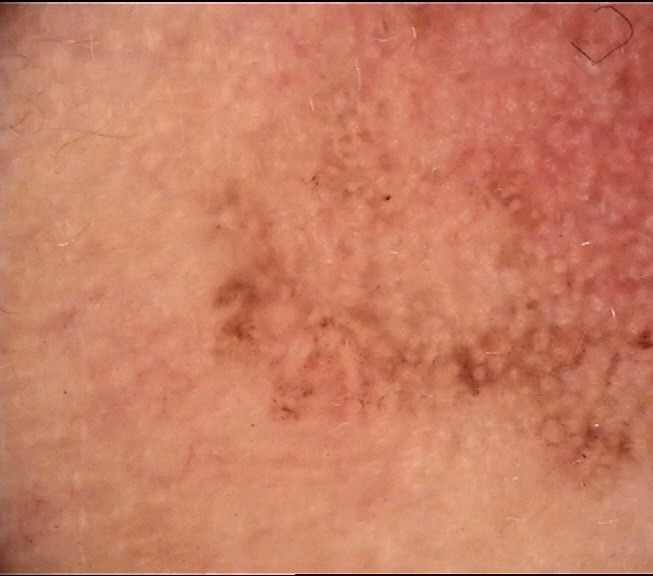A dermoscopic photograph of a skin lesion.
Classified as a keratinocytic, indeterminate lesion — an actinic keratosis.